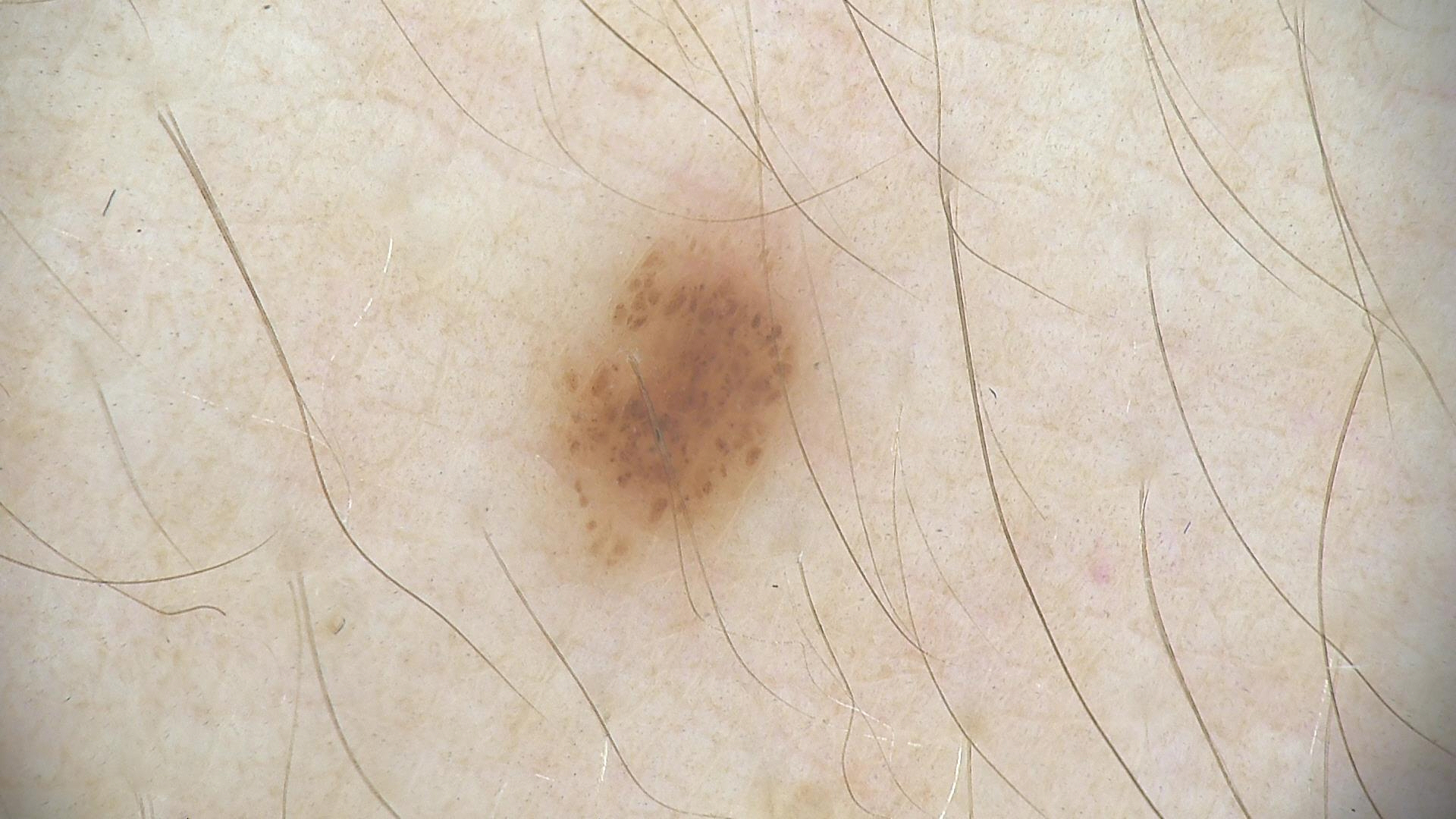Impression: Consistent with a dysplastic junctional nevus.